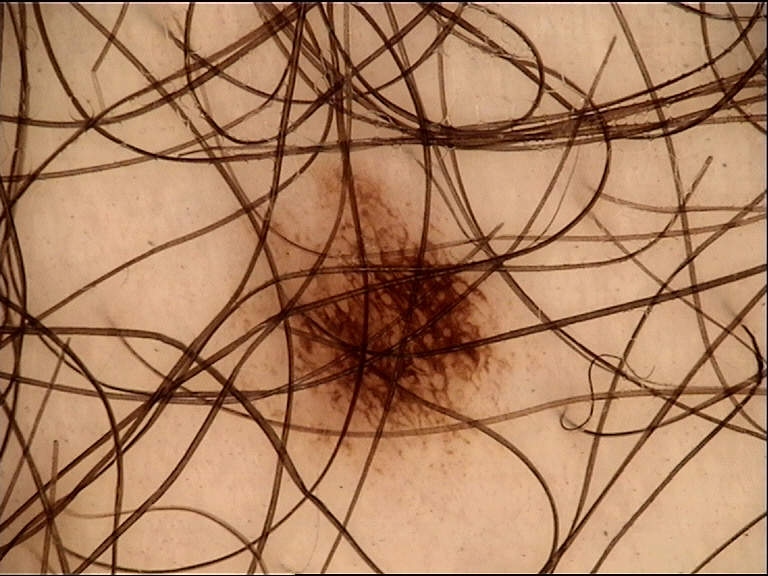diagnosis:
  name: dysplastic junctional nevus
  code: jd
  malignancy: benign
  super_class: melanocytic
  confirmation: expert consensus